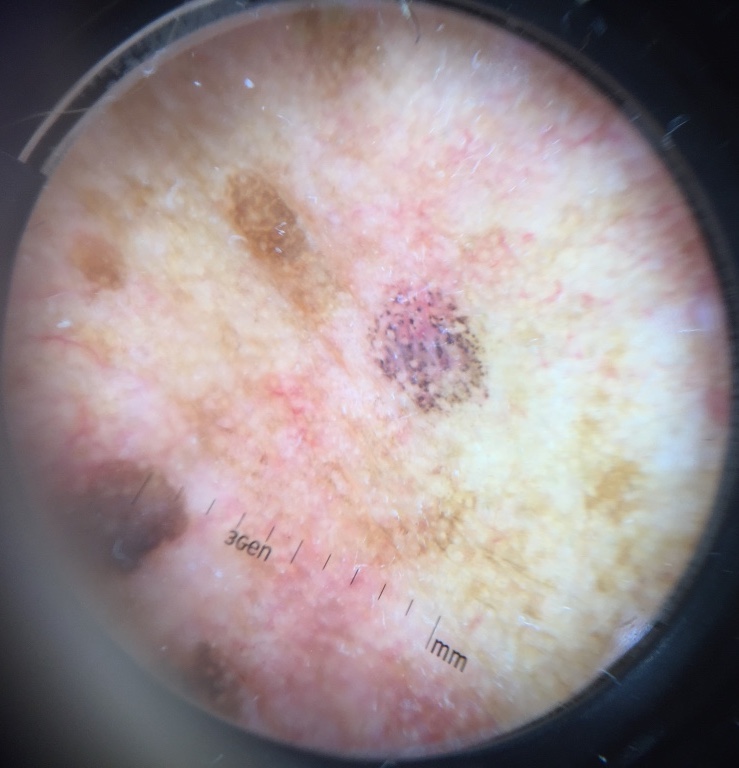diagnostic label: basal cell carcinoma (biopsy-proven).